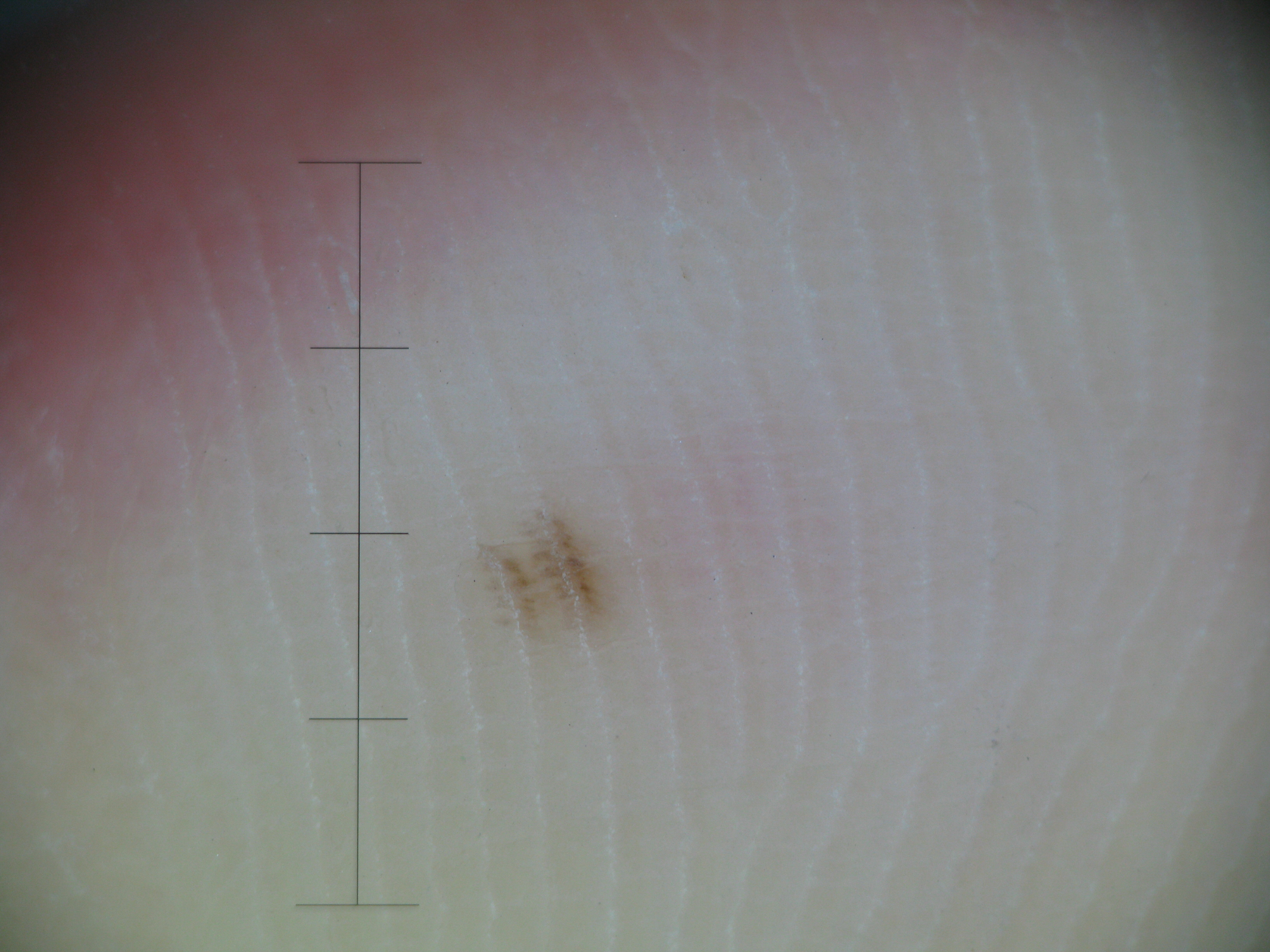  diagnosis:
    name: acral junctional nevus
    code: ajb
    malignancy: benign
    super_class: melanocytic
    confirmation: expert consensus